An image taken at a distance · the patient described the issue as a rash · the condition has been present for more than one year · the lesion is described as rough or flaky · the patient reports itching: 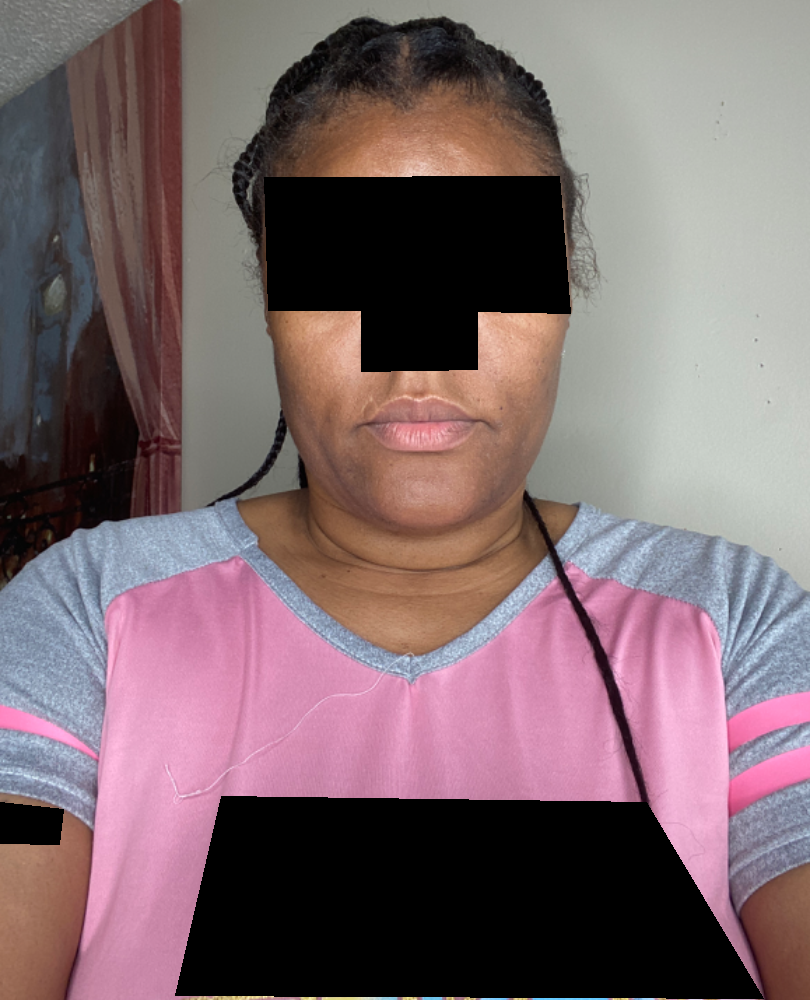No discernible skin pathology was identified on dermatologist review.